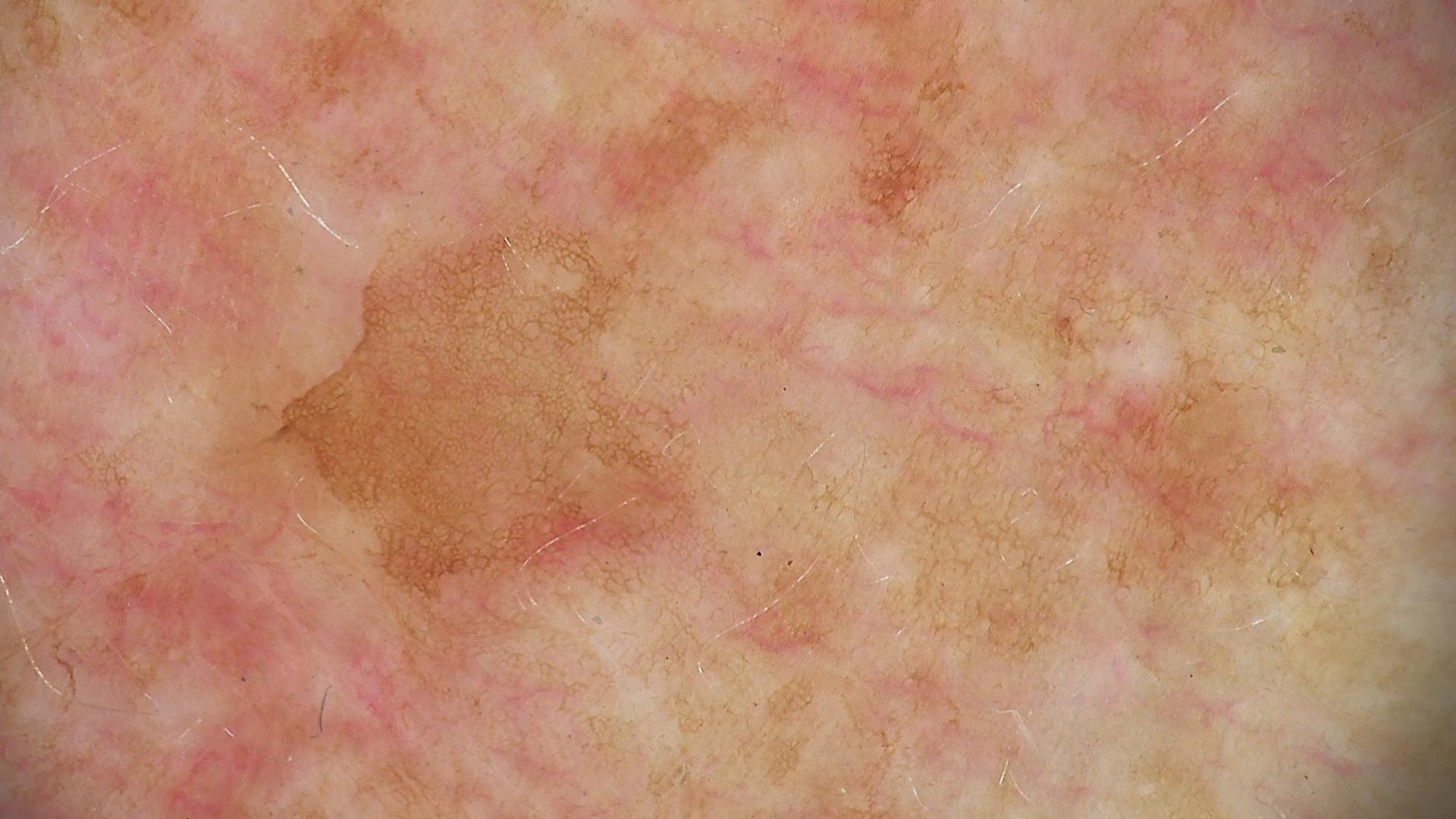assessment = solar lentigo (expert consensus).